Dermoscopy of a skin lesion.
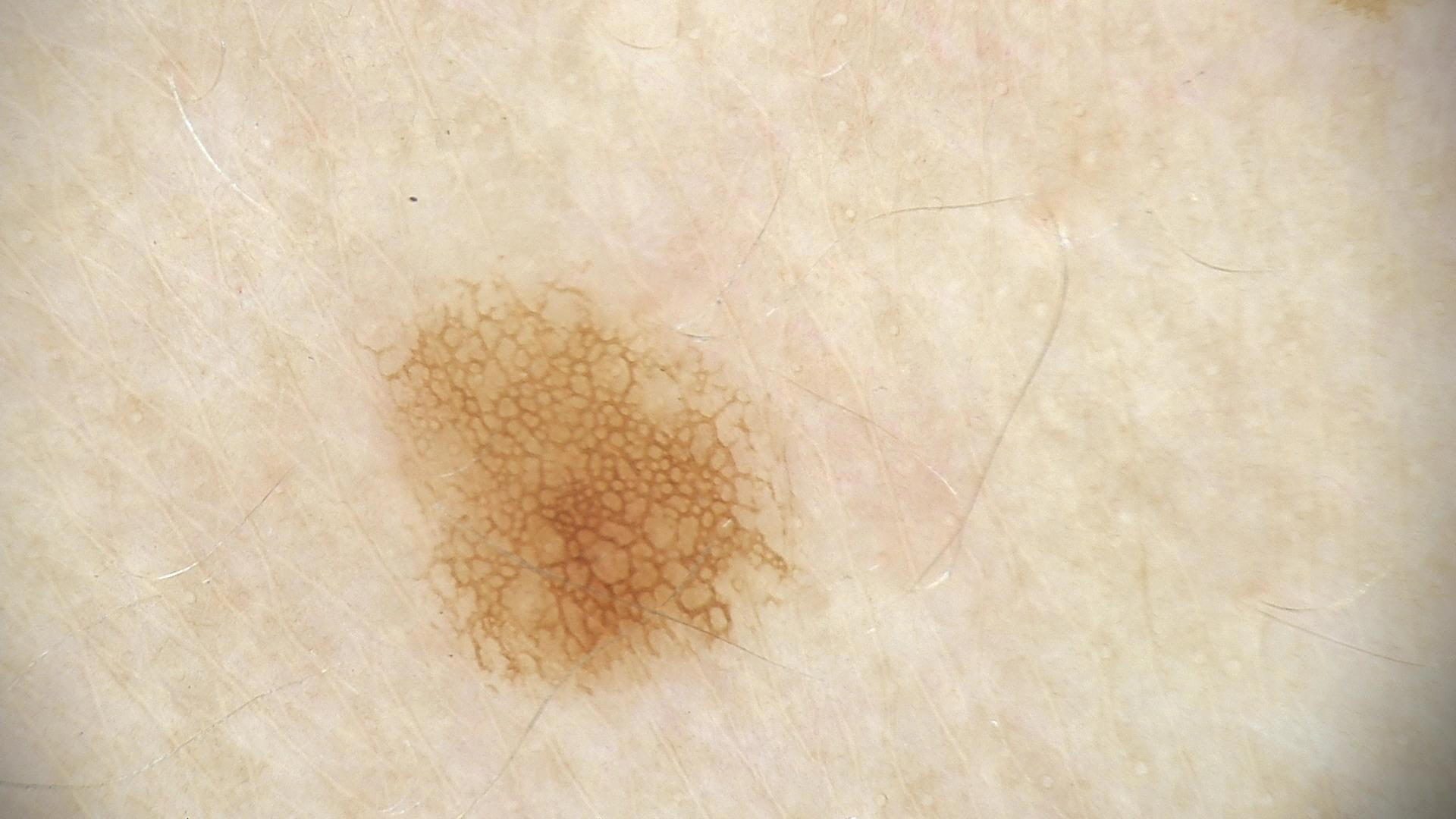diagnostic label = junctional nevus (expert consensus).